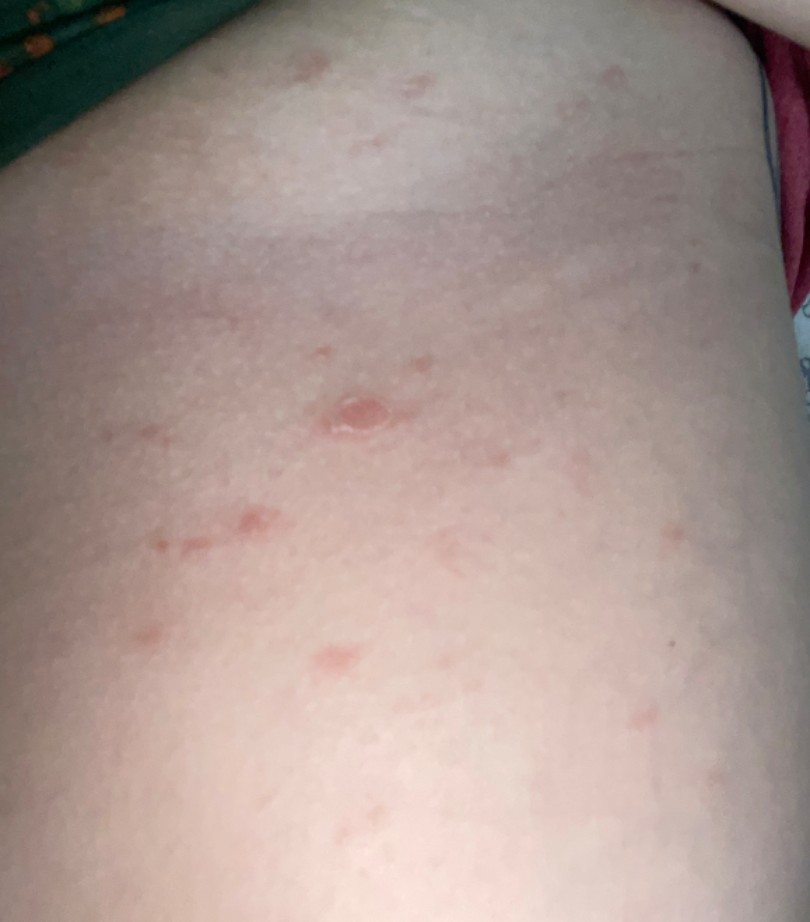  patient_category: a rash
  patient: female, age 18–29
  body_site: front of the torso
  systemic_symptoms:
    - chills
    - joint pain
    - shortness of breath
    - fatigue
  skin_tone:
    fitzpatrick: III
    monk_skin_tone: 2
  symptoms:
    - pain
    - enlargement
    - burning
    - itching
  texture:
    - raised or bumpy
    - rough or flaky
  shot_type: close-up
  duration: one to four weeks
  differential:
    tied_lead:
      - Pityriasis rosea
      - Acute and chronic dermatitis
      - Pityriasis lichenoides